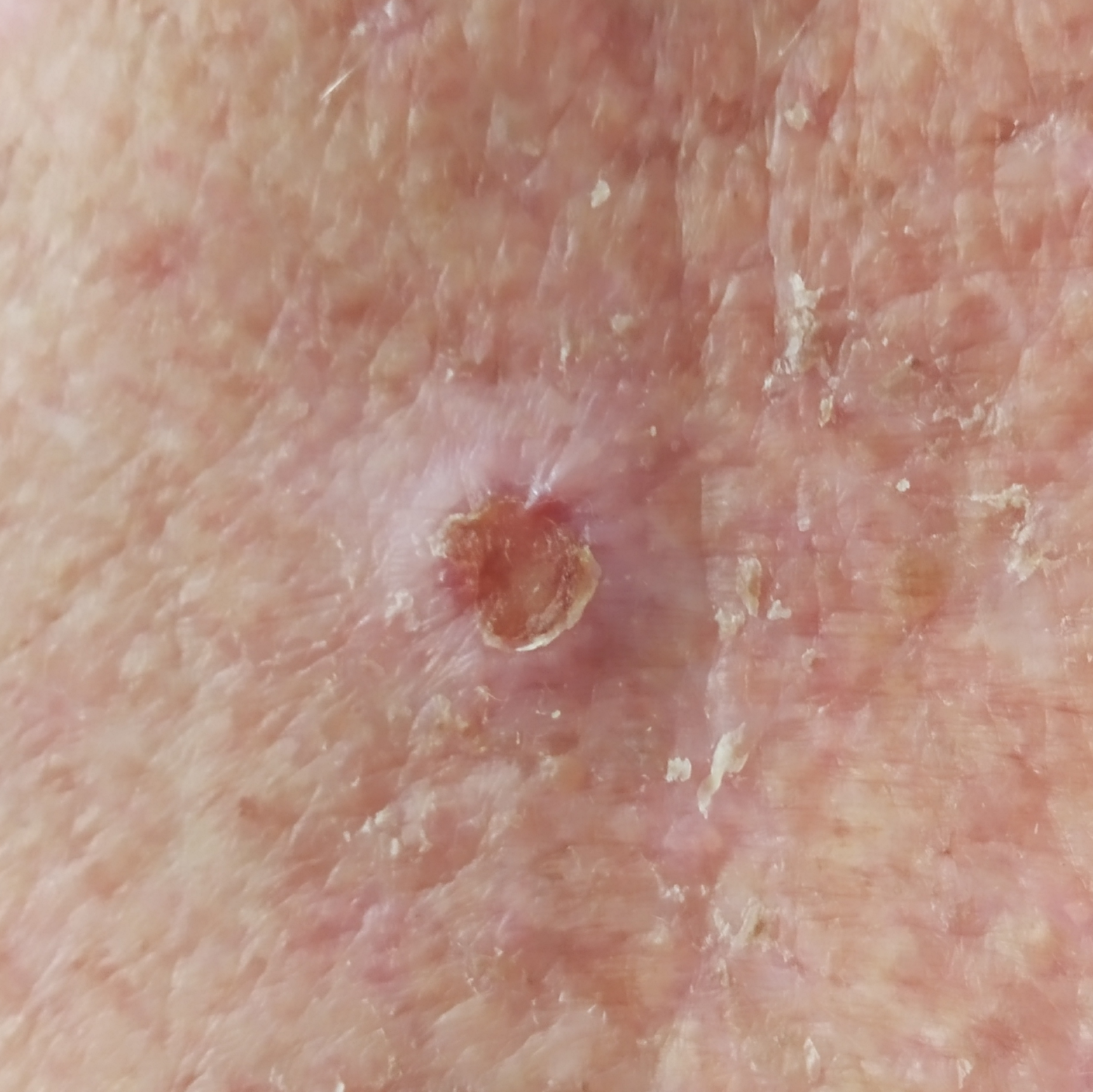<case>
  <lesion_location>the chest</lesion_location>
  <lesion_size>
    <diameter_1_mm>22.0</diameter_1_mm>
    <diameter_2_mm>15.0</diameter_2_mm>
  </lesion_size>
  <symptoms>
    <present>bleeding, growth, itching, elevation, pain</present>
    <absent>change in appearance</absent>
  </symptoms>
  <diagnosis>
    <name>basal cell carcinoma</name>
    <code>BCC</code>
    <malignancy>malignant</malignancy>
    <confirmation>histopathology</confirmation>
  </diagnosis>
</case>